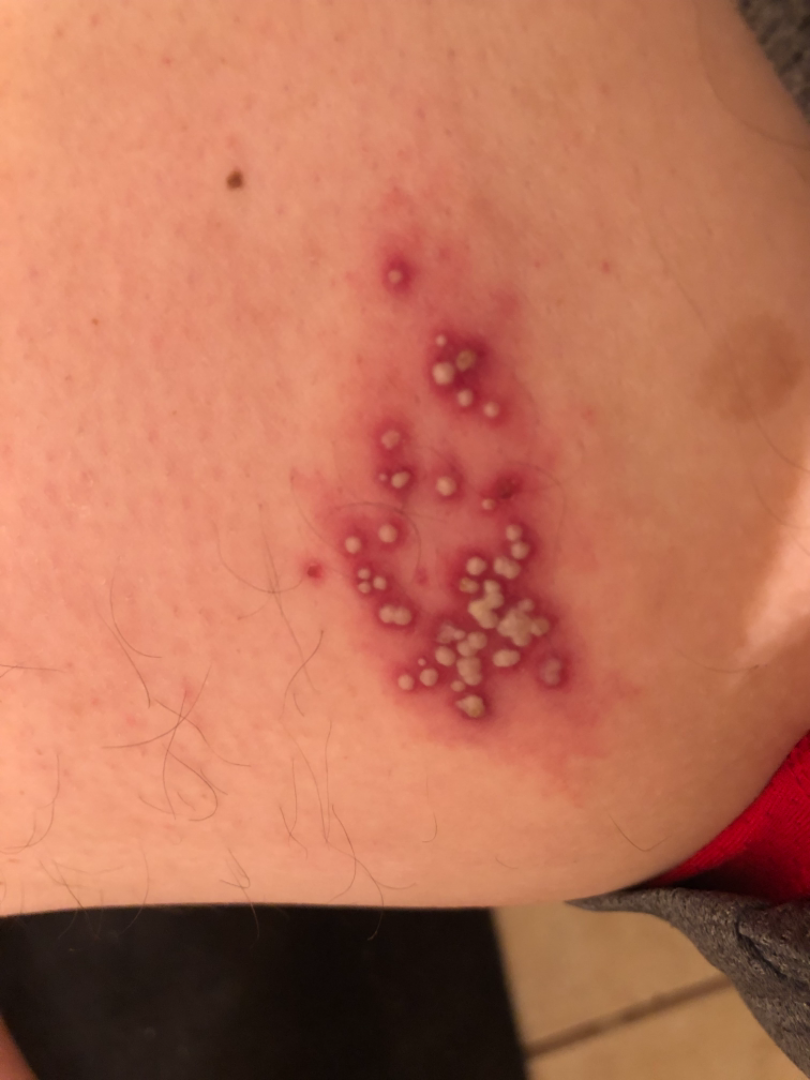lesion texture: raised or bumpy
contributor: male
body site: leg
view: close-up
patient describes the issue as: a rash
skin tone: Fitzpatrick phototype II
symptom duration: less than one week
patient-reported symptoms: burning, itching, pain, bothersome appearance and darkening
differential diagnosis: most likely Herpes Simplex; an alternative is Herpes Zoster; less probable is Psoriasis